A female subject aged around 70 · a dermoscopic close-up of a skin lesion.
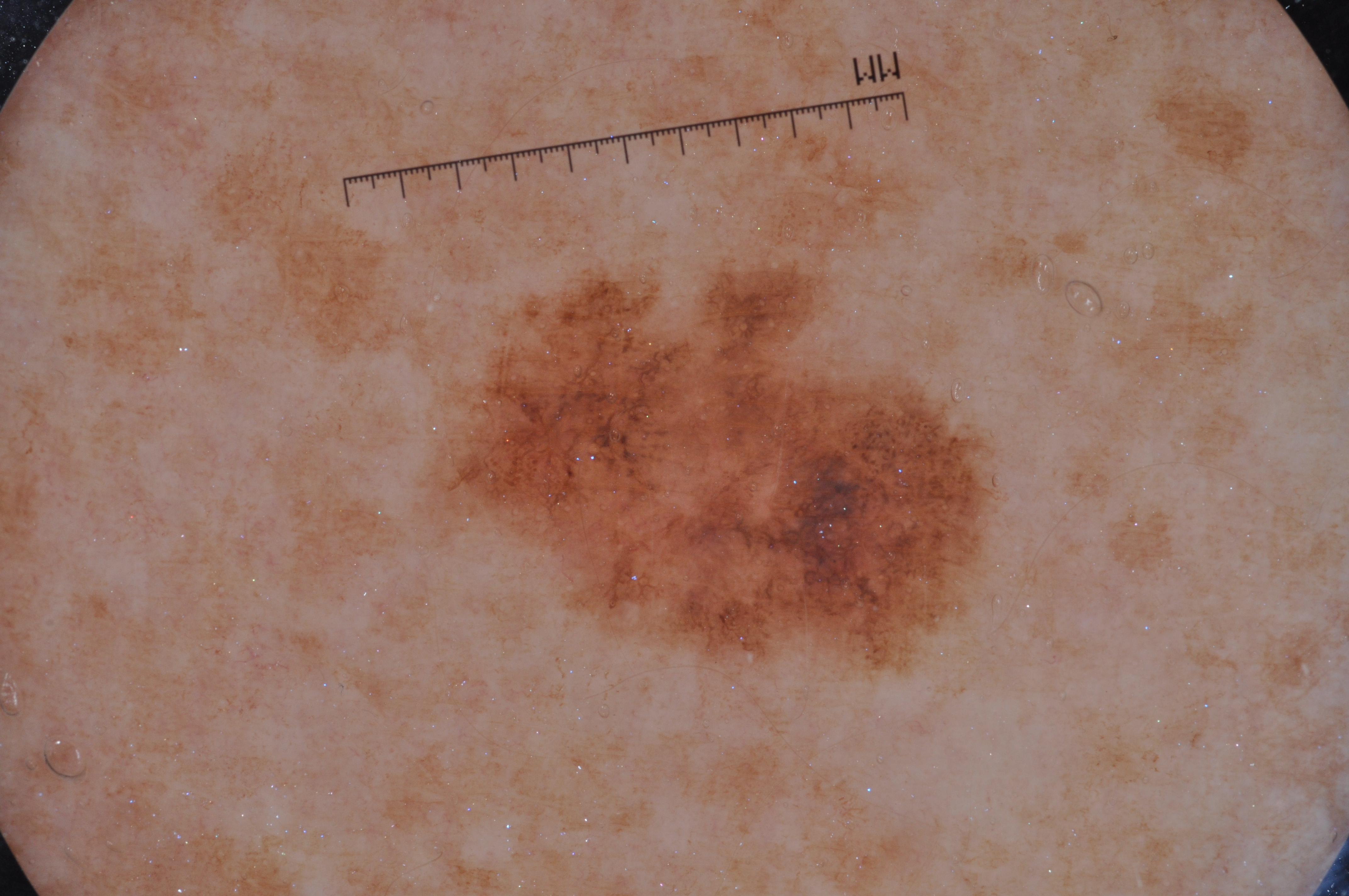The dermoscopic pattern shows pigment network and milia-like cysts. The lesion takes up a moderate portion of the field. The lesion spans (443, 273, 991, 665). Histopathologically confirmed as a melanoma.